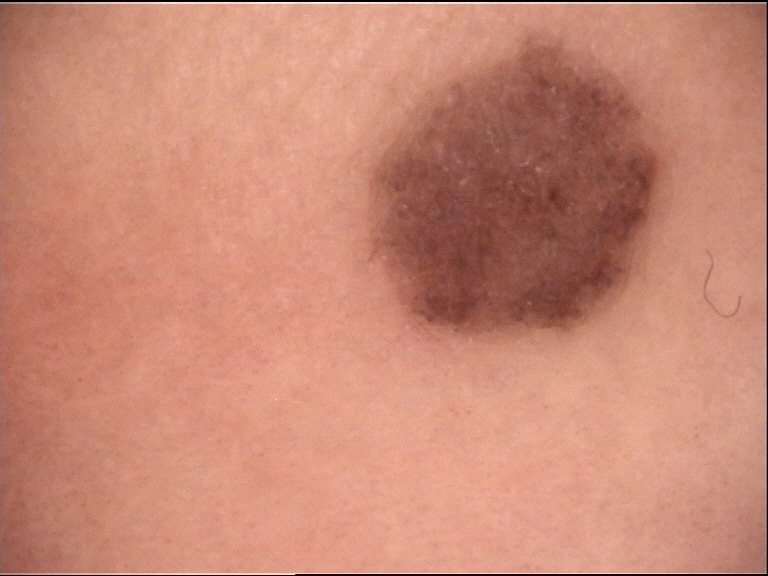Conclusion: The diagnosis was a compound nevus.